The photo was captured at a distance · the subject is female · the leg is involved: 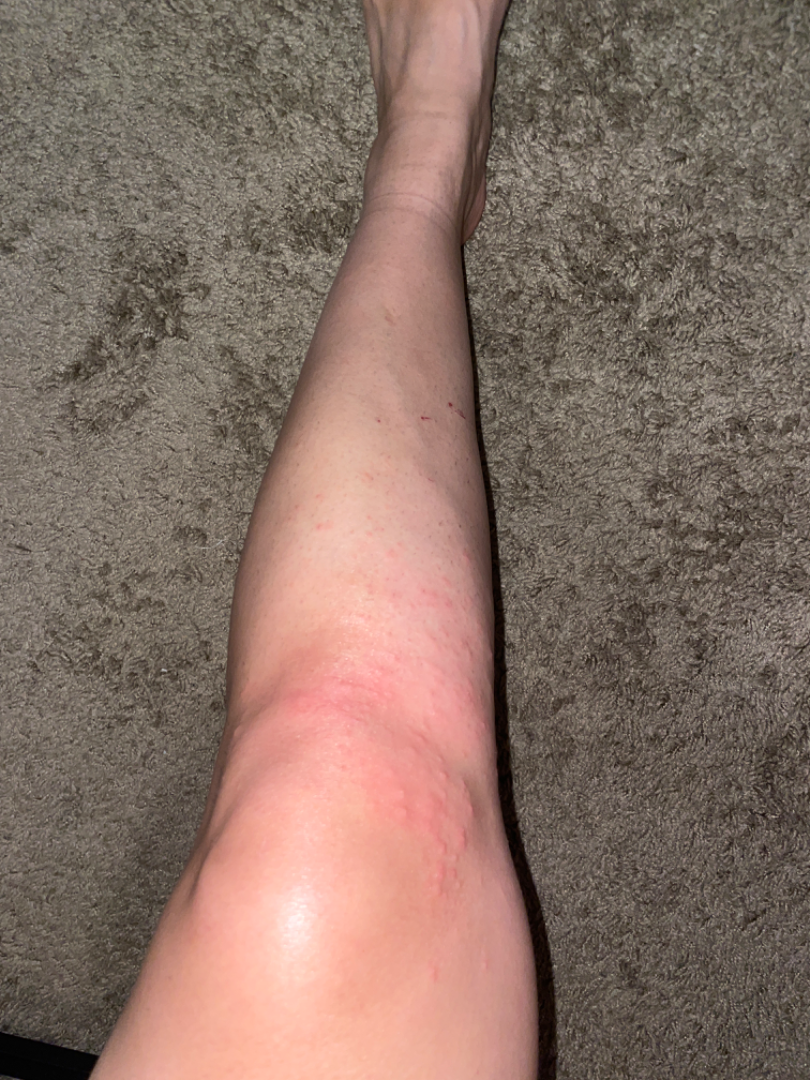Patient information:
The contributor notes the condition has been present for about one day. The patient considered this a rash. Reported lesion symptoms include itching and burning. The contributor notes the lesion is raised or bumpy and fluid-filled.
Review:
Reviewed remotely by one dermatologist: most consistent with Eczema; an alternative is Insect Bite; also raised was Allergic Contact Dermatitis.